The photograph is a close-up of the affected area: 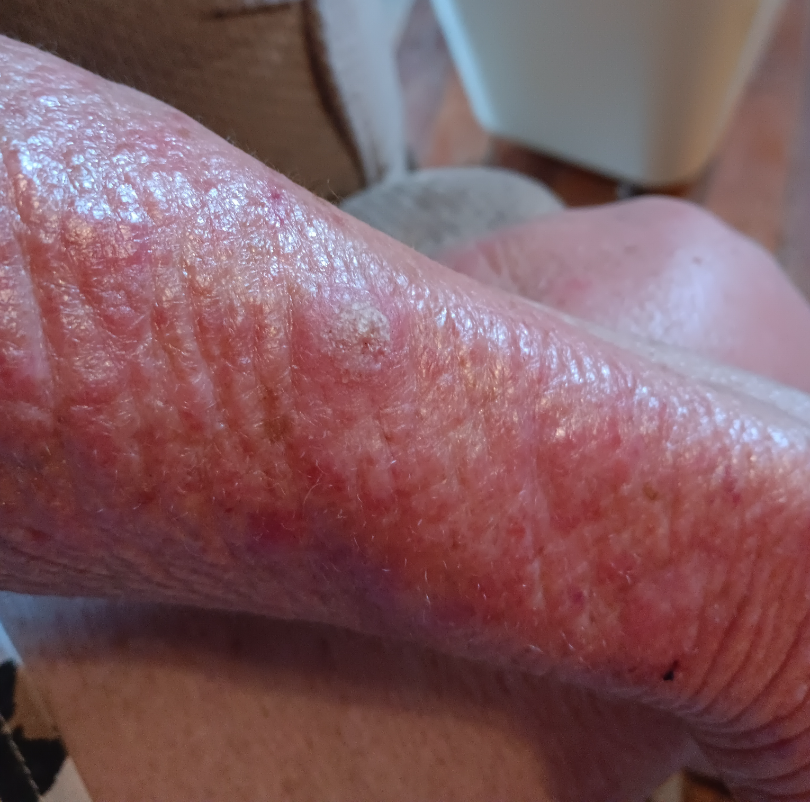On photographic review by a dermatologist, most consistent with SCC/SCCIS.